Reported duration is about one day. The contributor is a female aged 70–79. The photograph is a close-up of the affected area. The patient considered this a rash. The affected area is the leg and front of the torso. The patient indicates the lesion is raised or bumpy: 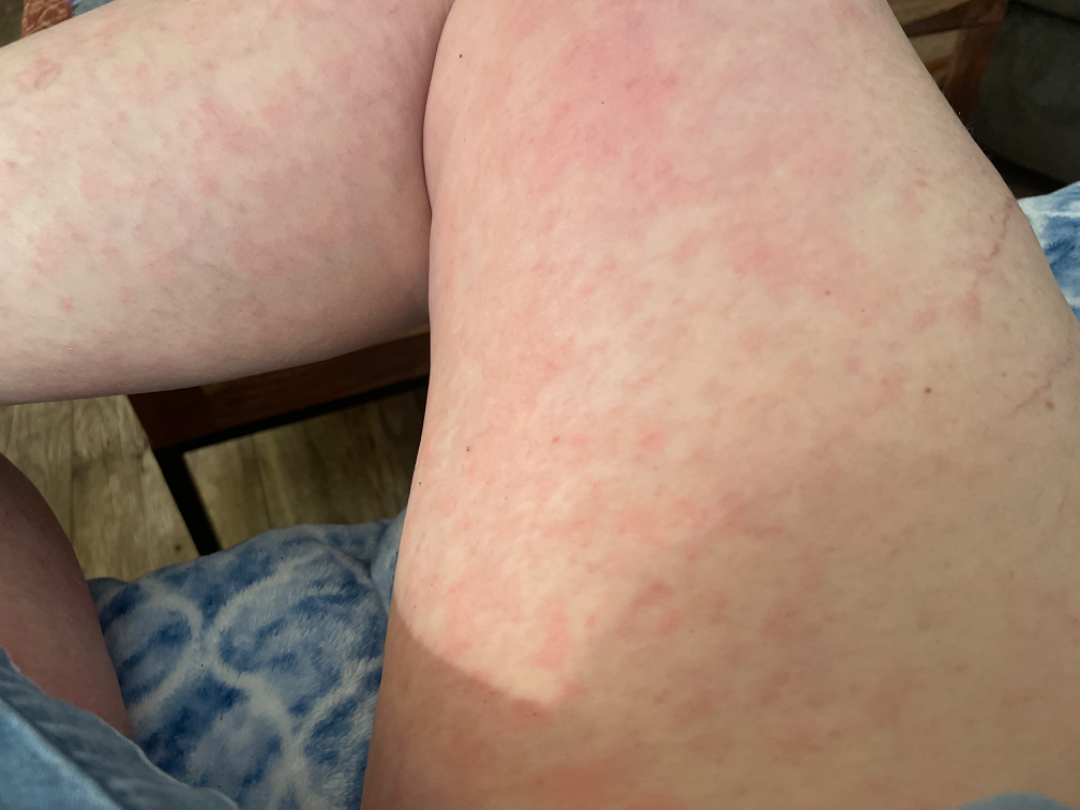differential:
  leading:
    - Drug Rash
  considered:
    - Viral Exanthem
  unlikely:
    - Urticaria